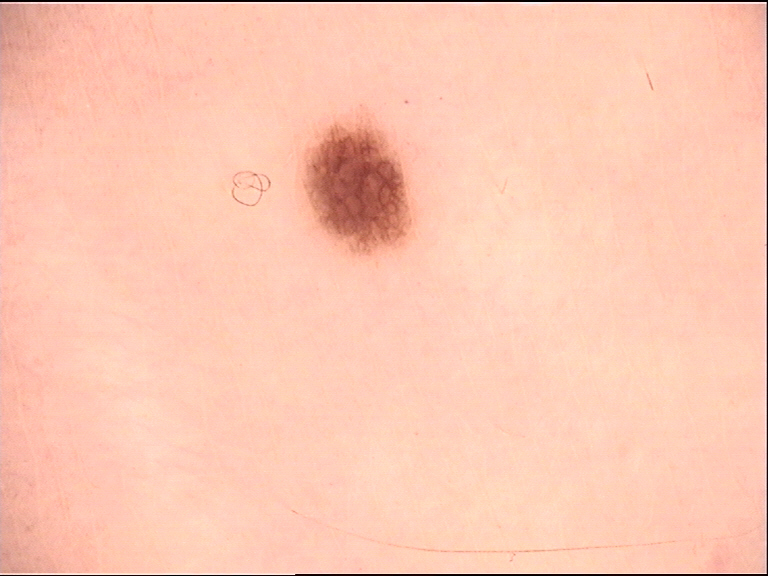imaging: dermatoscopy
diagnosis: dysplastic junctional nevus (expert consensus)